A dermoscopic photograph of a skin lesion: 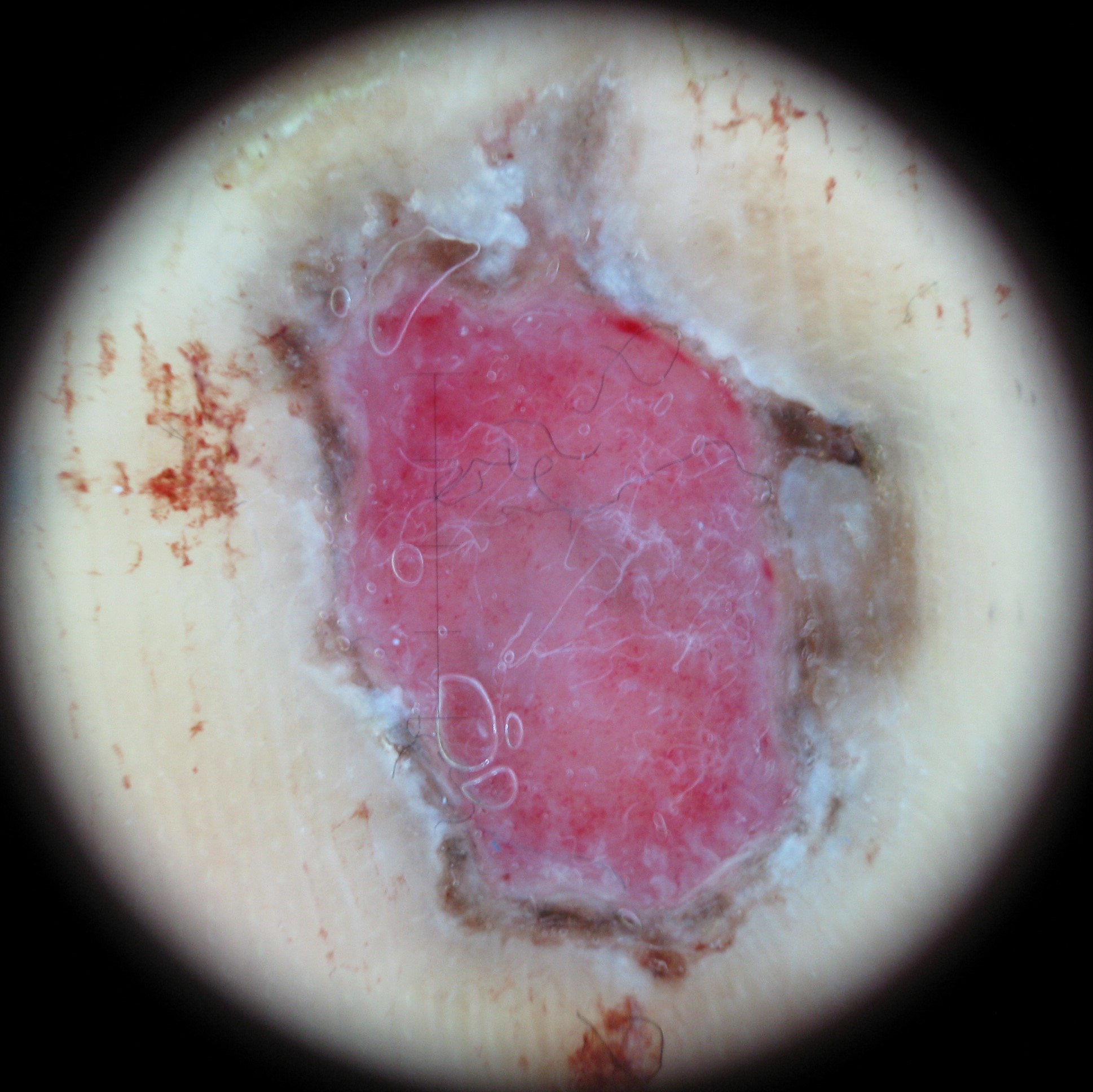| feature | finding |
|---|---|
| class | acral nodular melanoma (biopsy-proven) |